The patient is a female roughly 70 years of age; a dermoscopic image of a skin lesion — 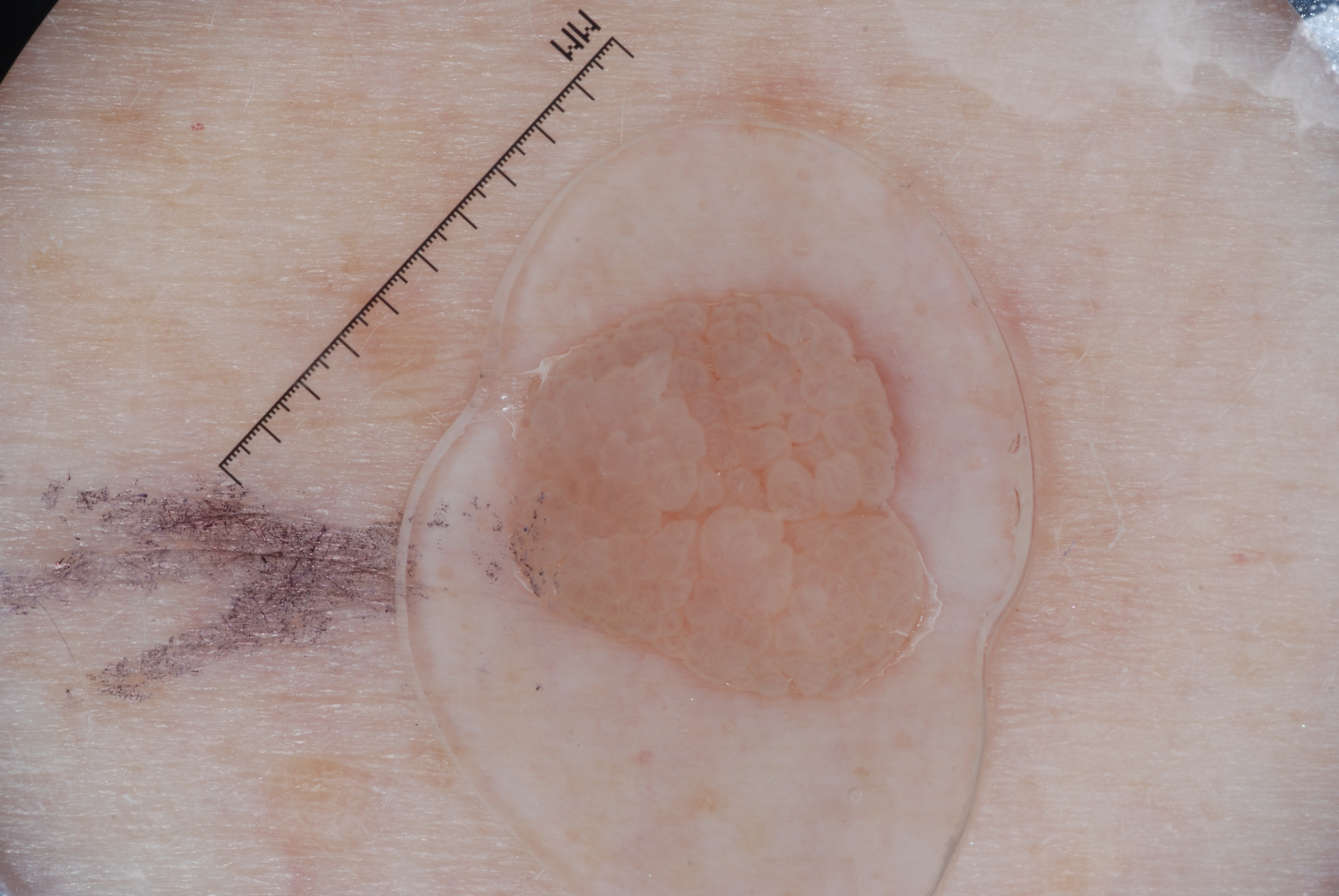dermoscopic features not present = pigment network, streaks, milia-like cysts, and negative network | lesion location = x1=491, y1=273, x2=920, y2=714 | assessment = a seborrheic keratosis, a benign skin lesion.